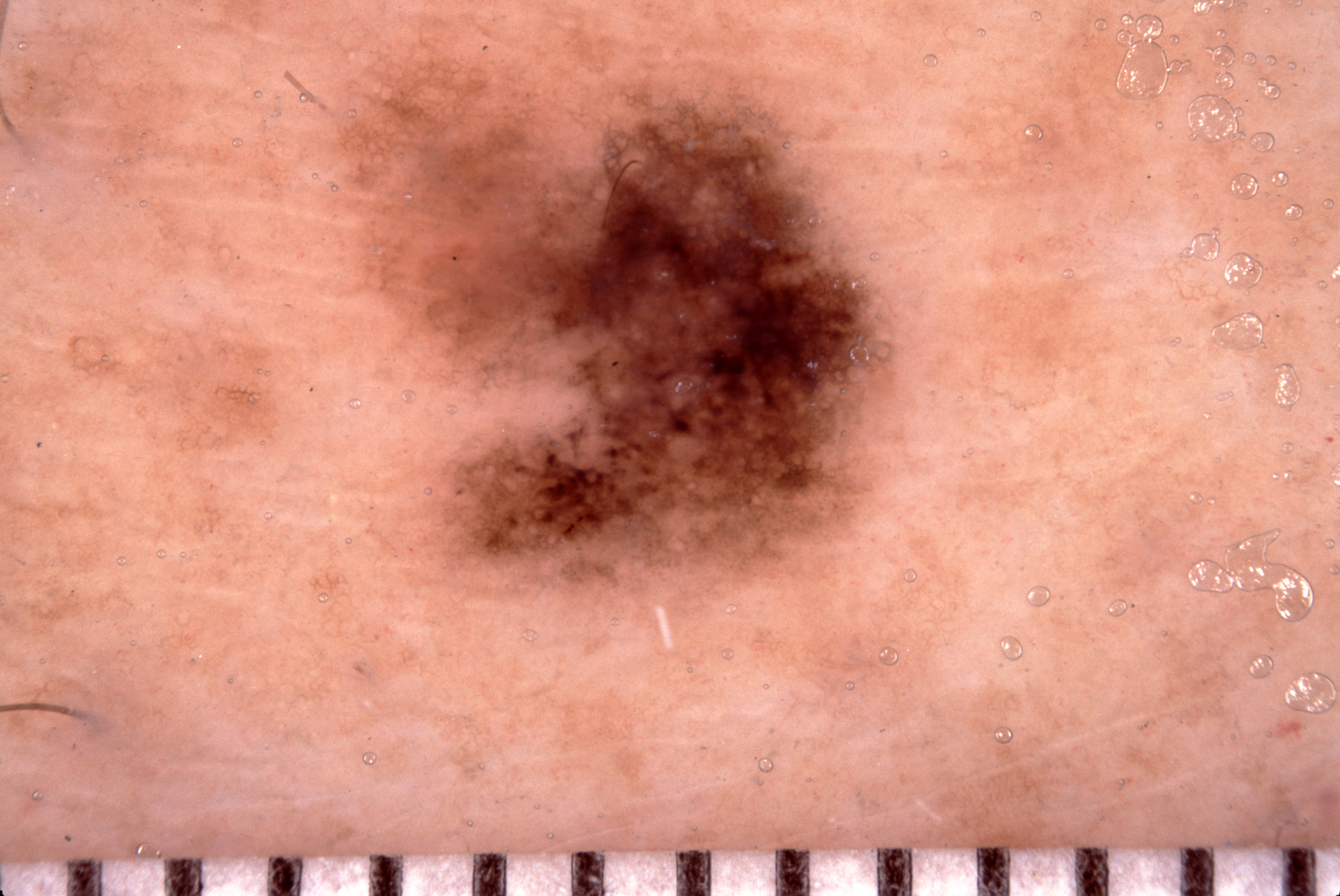image type = dermoscopic image | patient = female, aged around 40 | lesion size = ~17% of the field | lesion location = <bbox>337, 56, 898, 605</bbox> | features = pigment network; absent: streaks, milia-like cysts, and negative network | diagnosis = a melanoma, a malignancy.